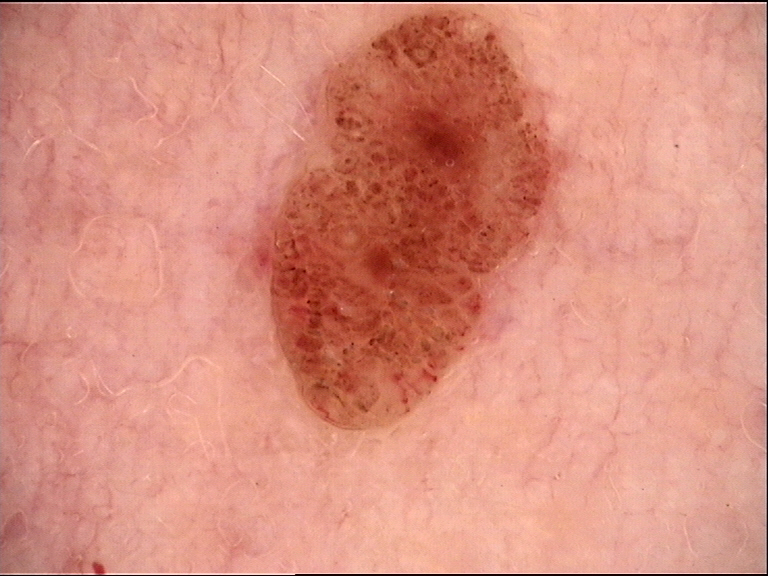image: dermoscopy
classification: banal
assessment: dermal nevus (expert consensus)